Close-up view — 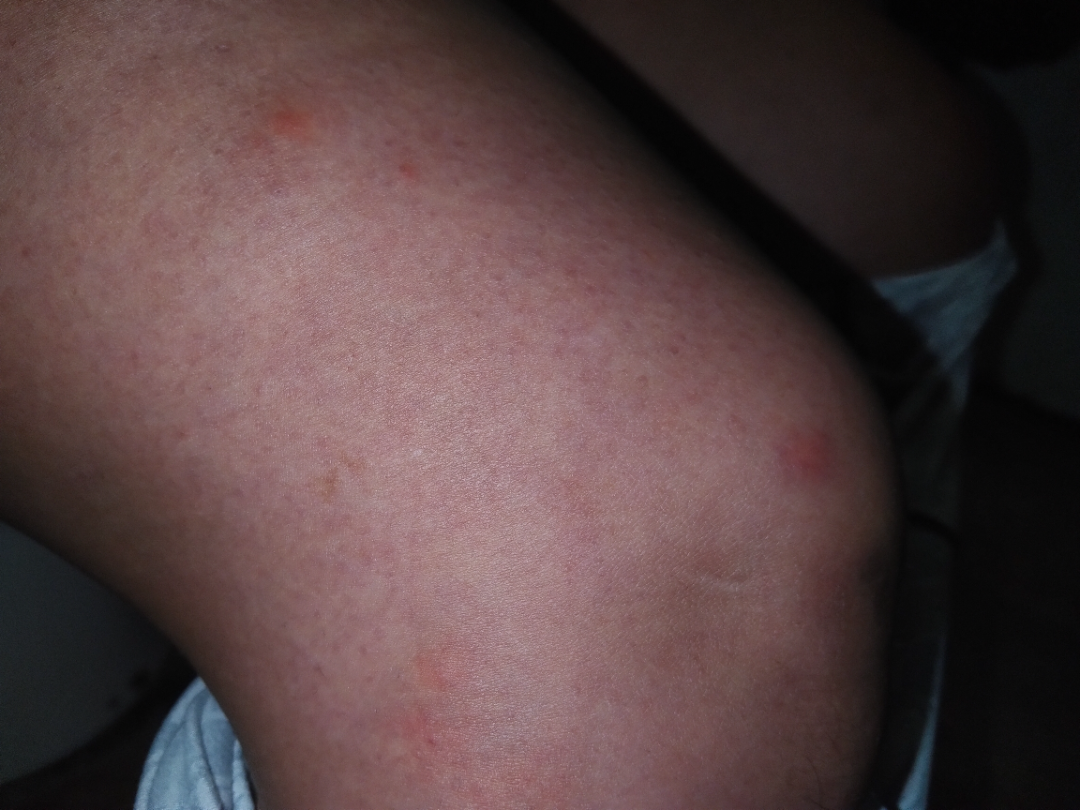Q: Could the case be diagnosed?
A: could not be assessed